A dermatoscopic image of a skin lesion.
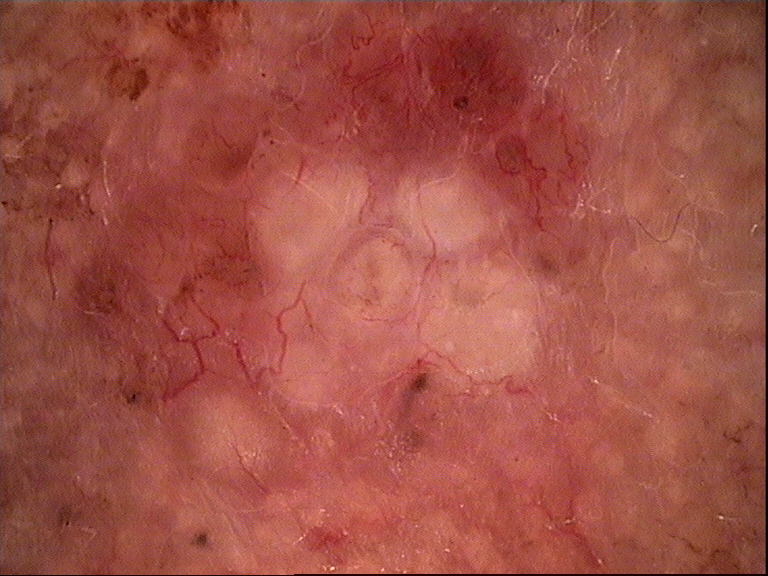Diagnosis: Confirmed on histopathology as a malignancy — a basal cell carcinoma.